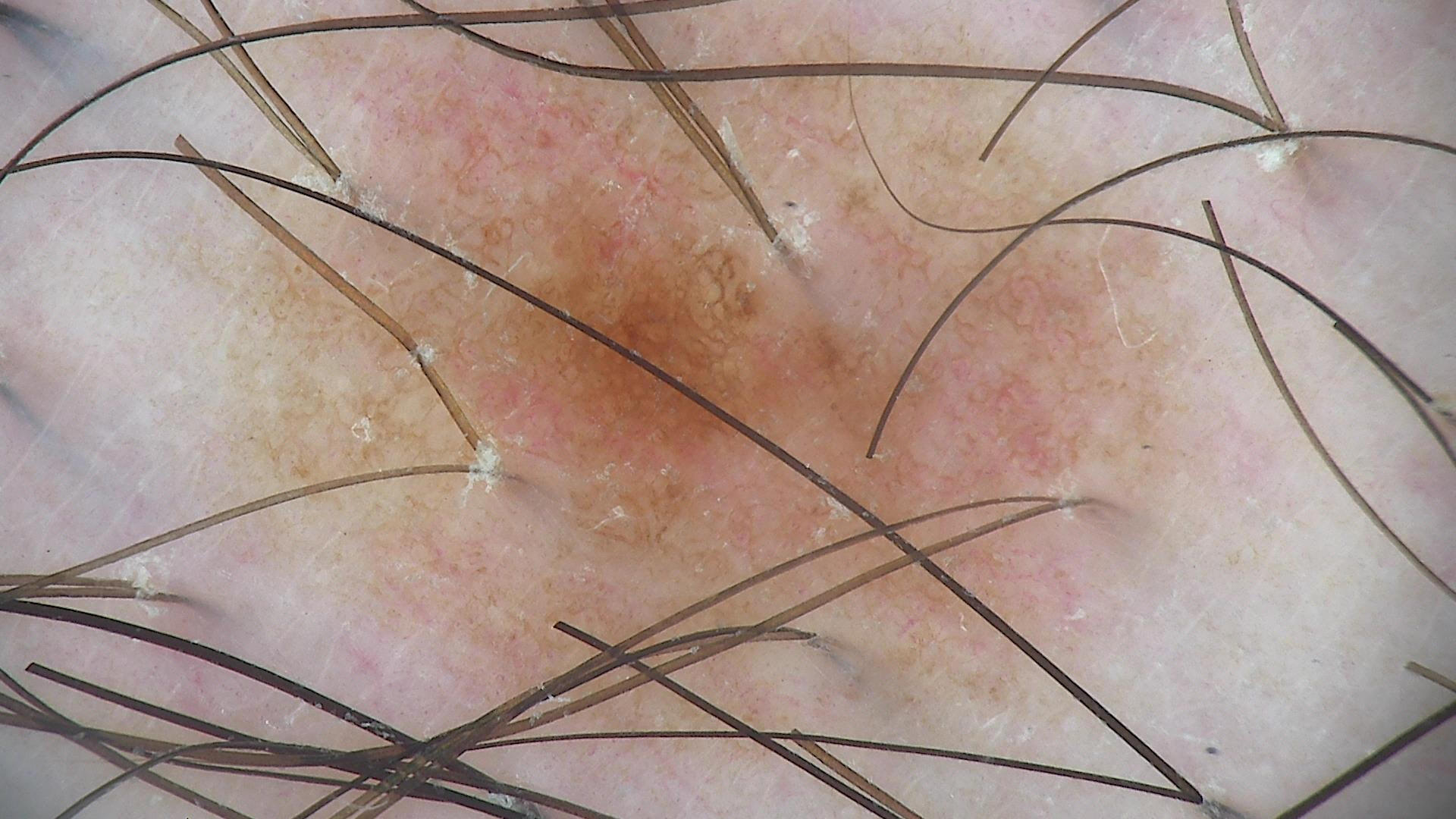Diagnosed as a compound nevus.